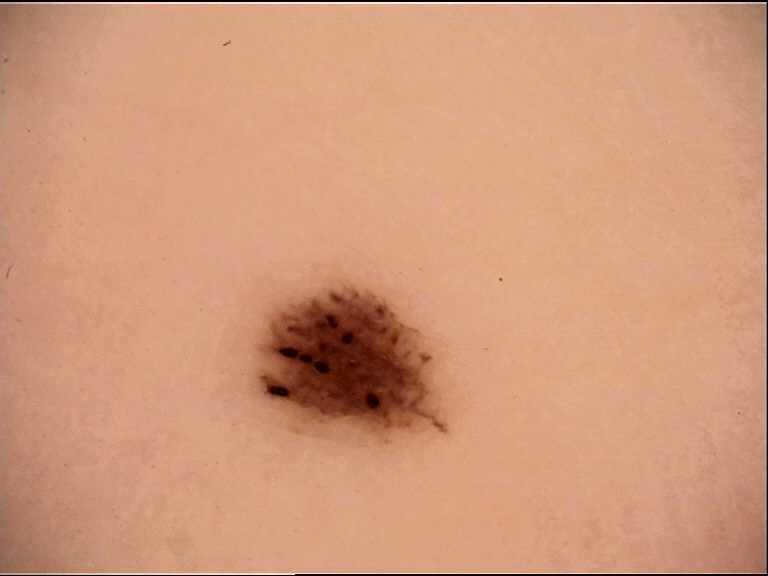Conclusion: Consistent with a benign lesion — an acral dysplastic junctional nevus.